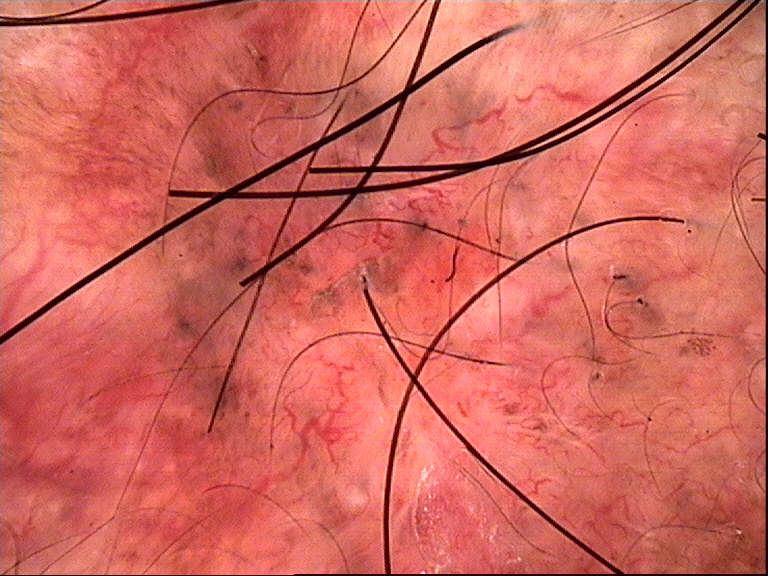- classification: keratinocytic
- diagnostic label: basal cell carcinoma (biopsy-proven)